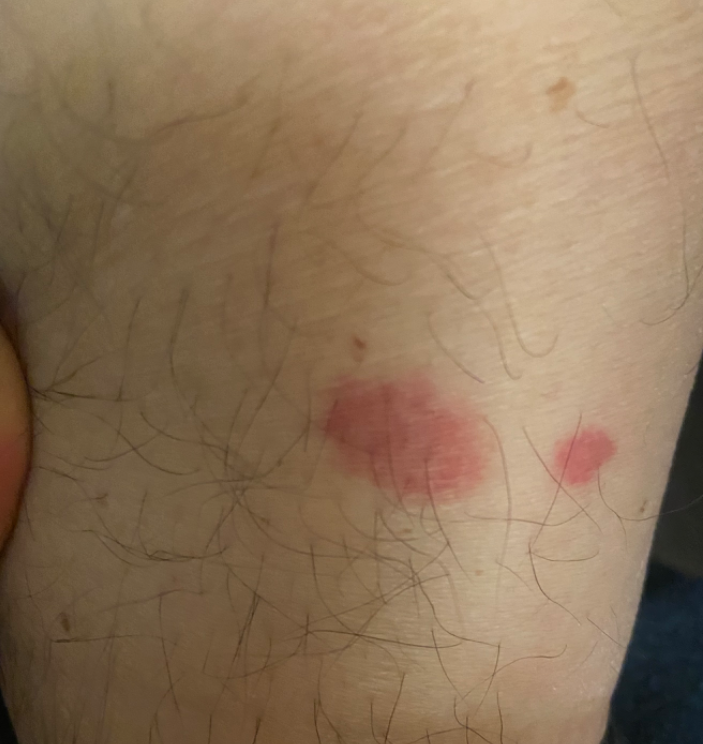Q: What is the framing?
A: close-up
Q: Where on the body?
A: leg
Q: What conditions are considered?
A: favoring Insect Bite; an alternative is Eczema; possibly Allergic Contact Dermatitis